The patient described the issue as a rash · the lesion is described as raised or bumpy · the photograph was taken at an angle · the lesion is associated with burning, pain, itching and bothersome appearance · present for about one day · the back of the torso is involved — 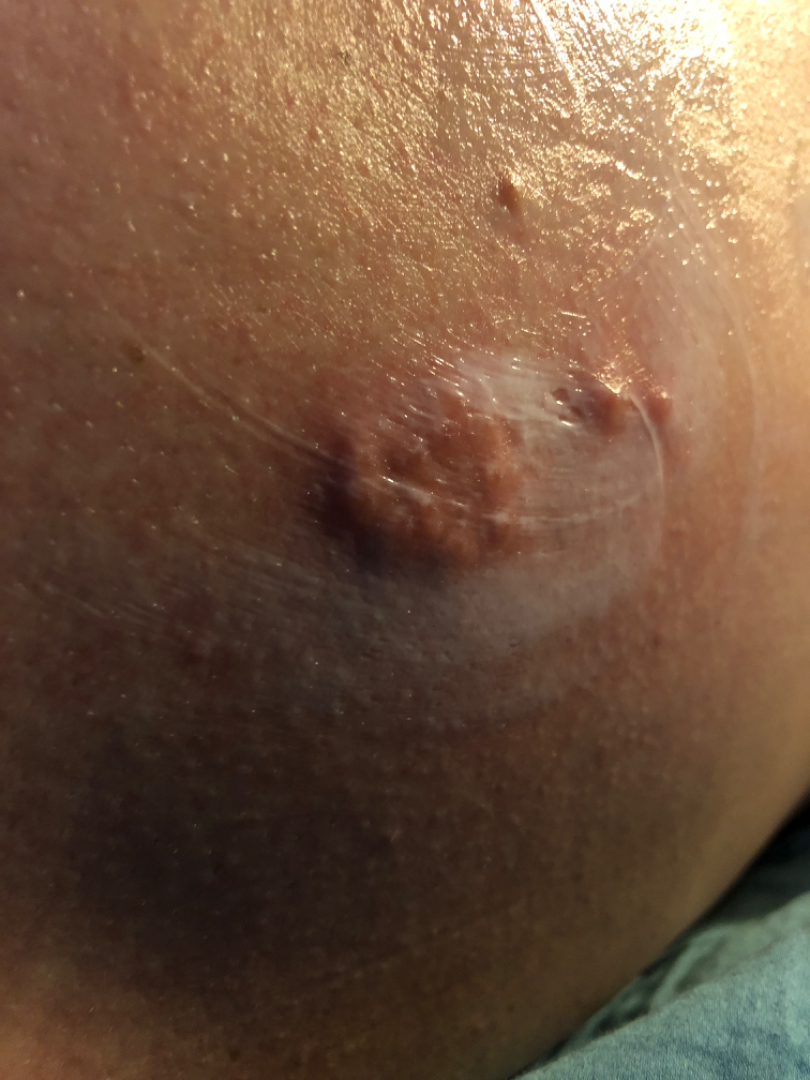<case>
  <differential>
    <leading>Folliculitis</leading>
    <considered>Herpes Simplex</considered>
    <unlikely>Deep fungal infection</unlikely>
  </differential>
</case>